The lesion involves the arm, a close-up photograph:
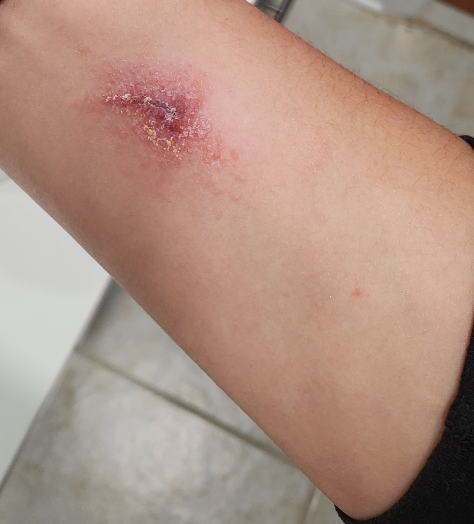onset: one to four weeks; reported symptoms: burning, enlargement, bothersome appearance and itching; surface texture: rough or flaky and raised or bumpy; self-categorized as: a rash; constitutional symptoms: none reported; impression: the differential, in no particular order, includes Impetigo and Allergic Contact Dermatitis.